A dermoscopic photograph of a skin lesion.
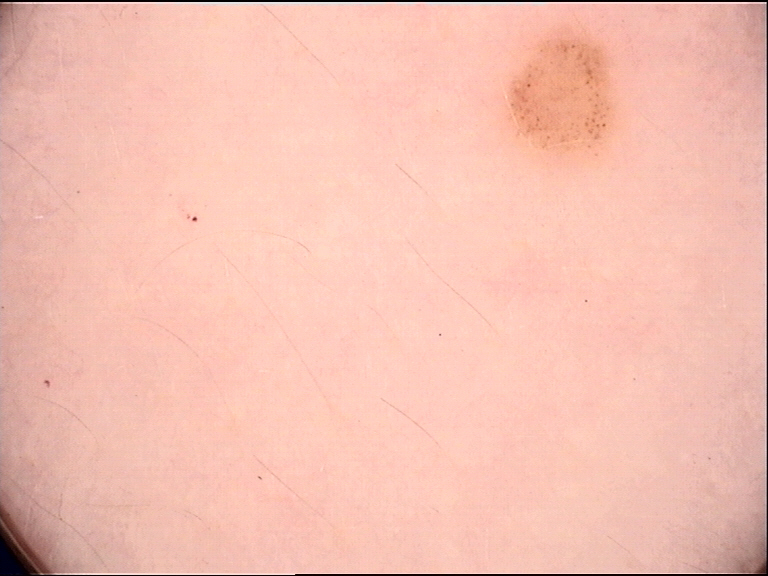Q: How is the lesion classified?
A: banal
Q: What is the diagnosis?
A: junctional nevus (expert consensus)